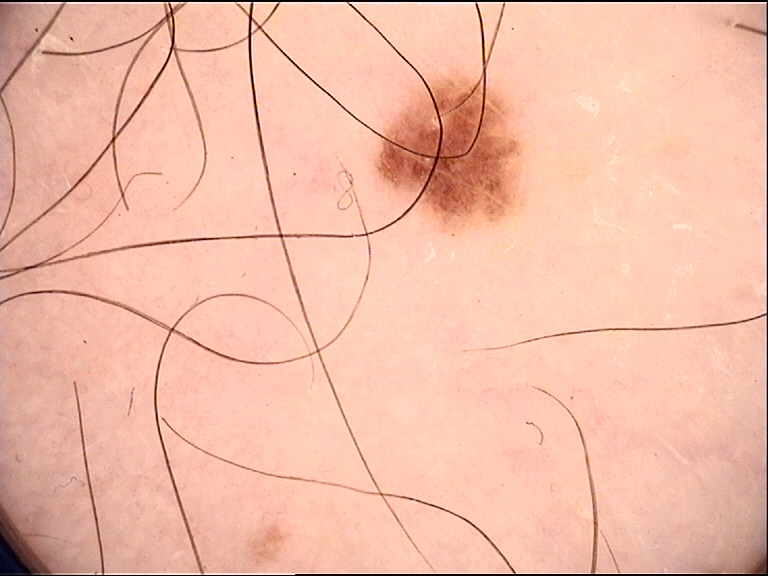Consistent with a dysplastic junctional nevus.